The contributor is 18–29, male · an image taken at an angle · the affected area is the arm.
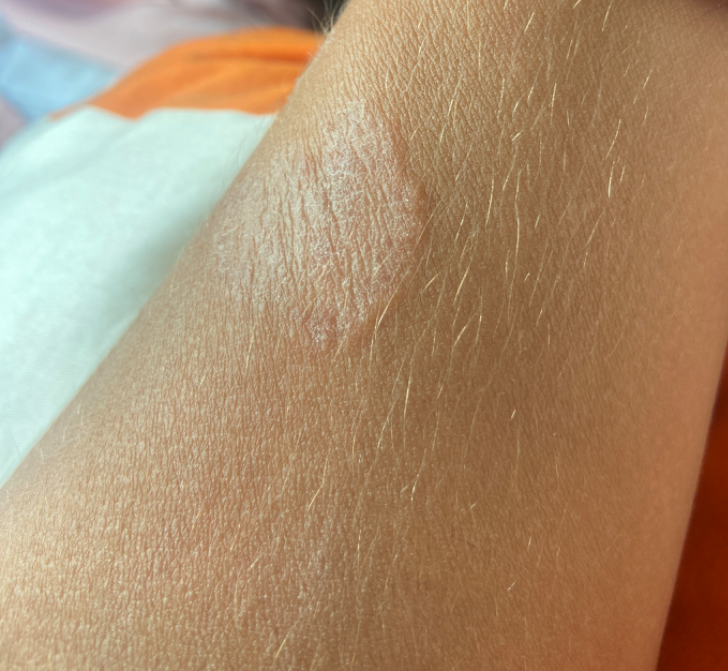{
  "symptoms": "itching",
  "systemic_symptoms": "none reported",
  "patient_category": "a rash",
  "texture": "rough or flaky",
  "skin_tone": {
    "fitzpatrick": "IV"
  },
  "differential": {
    "tied_lead": [
      "Eczema",
      "Psoriasis"
    ]
  }
}